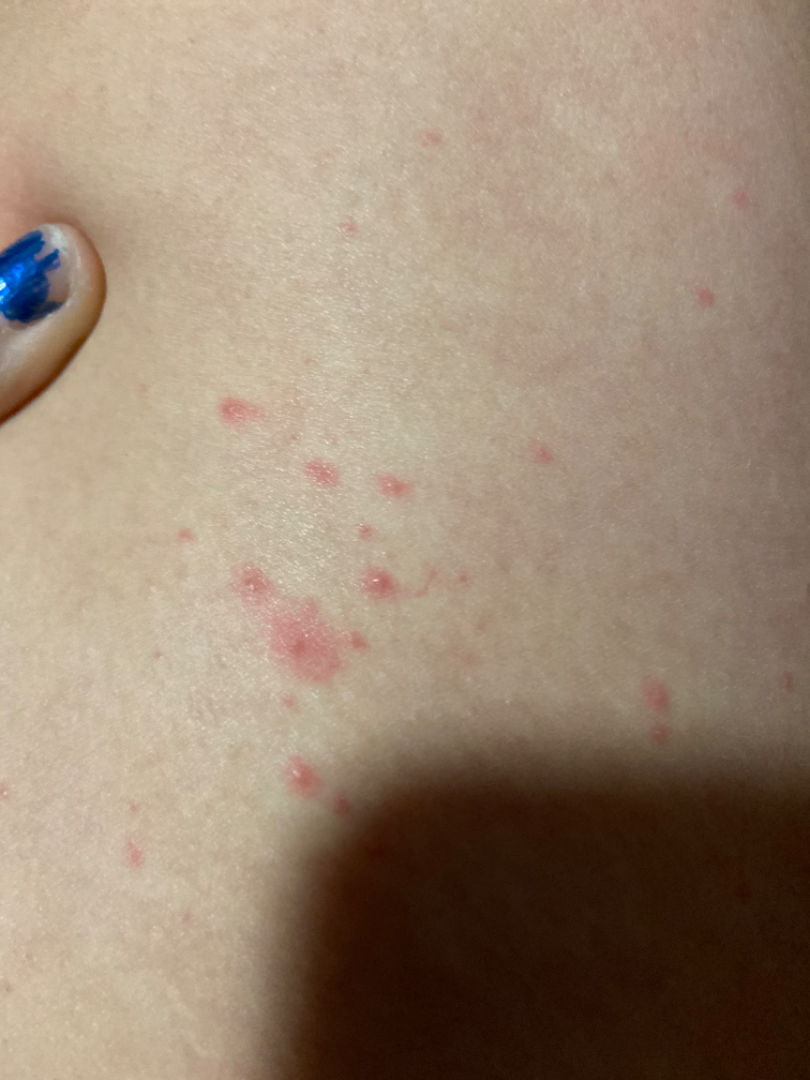Notes:
* differential · Urticaria, Insect Bite and Hypersensitivity were considered with similar weight